A dermoscopic close-up of a skin lesion: 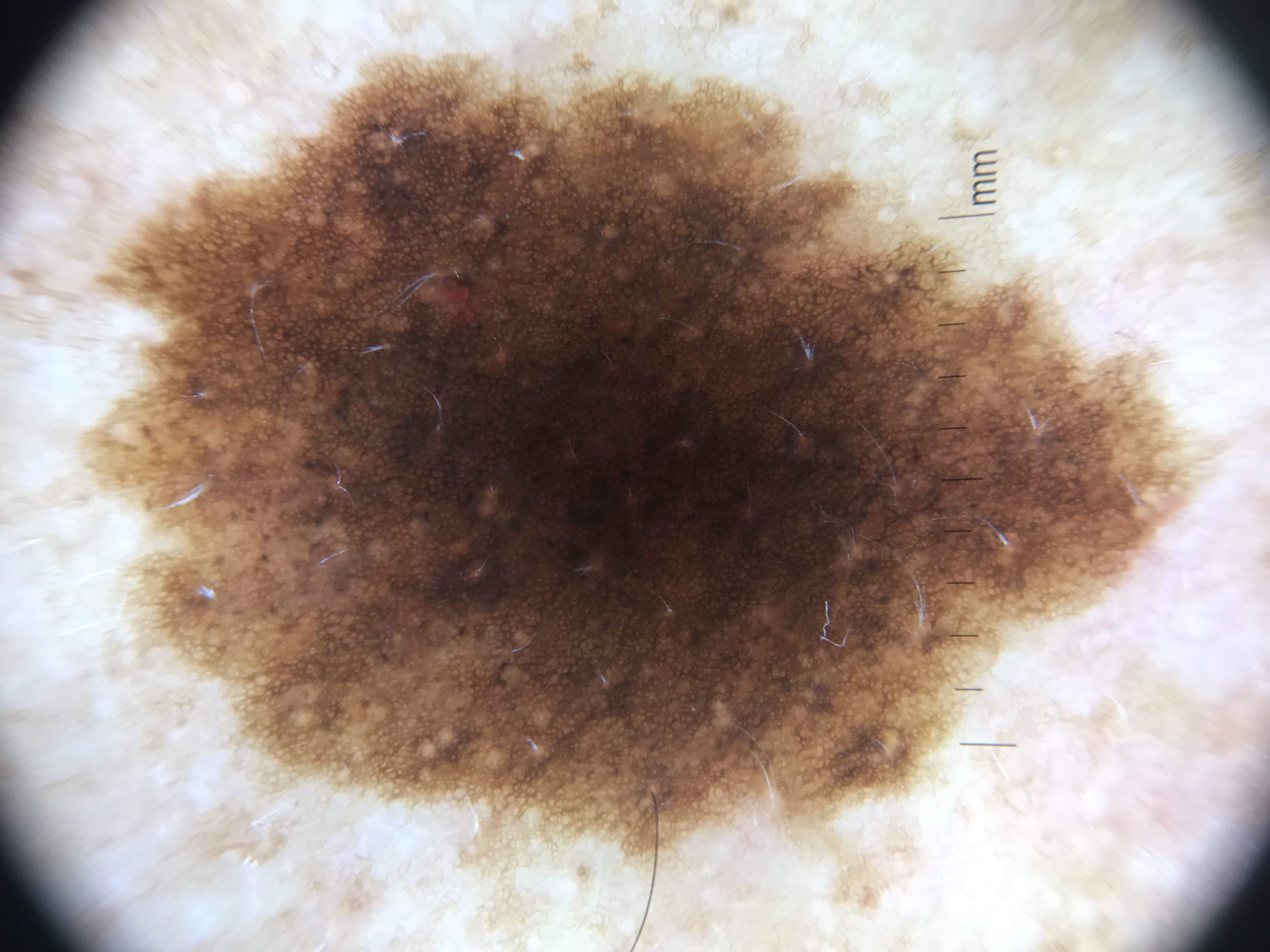diagnostic label: dysplastic compound nevus (expert consensus)